The lesion involves the leg · close-up view · female patient, age 30–39 — 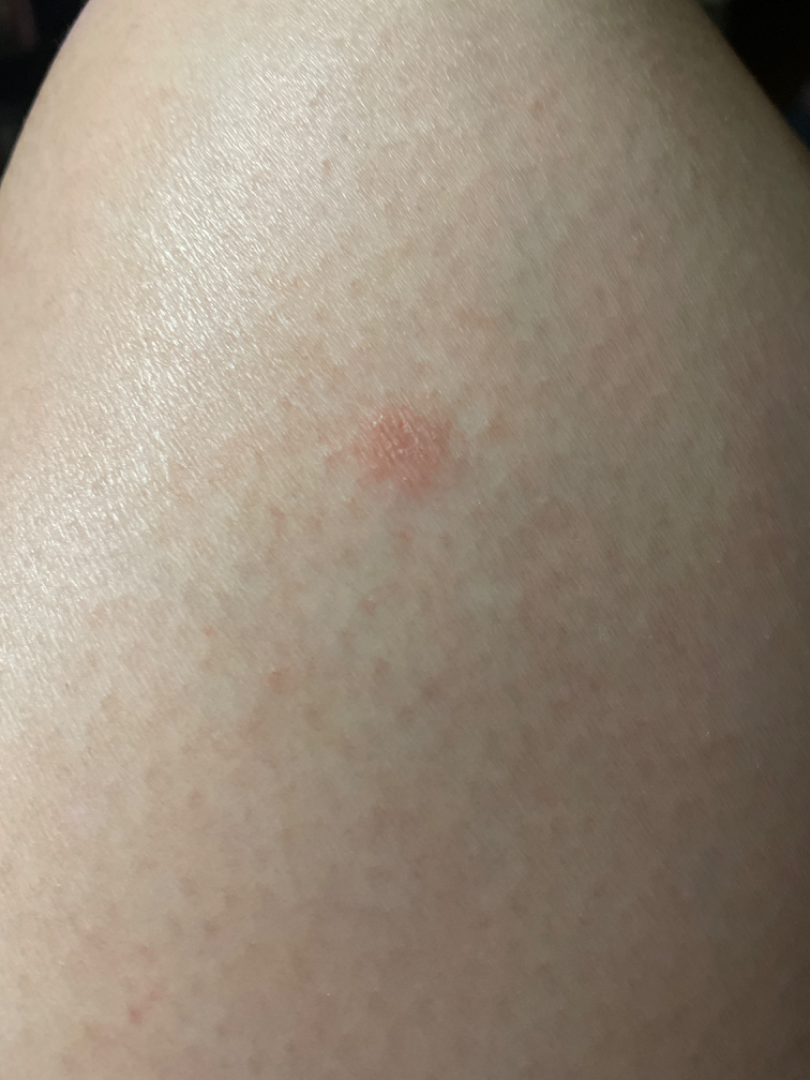{
  "differential": {
    "tied_lead": [
      "Keratosis",
      "Eczema"
    ],
    "unlikely": [
      "Actinic Keratosis"
    ]
  }
}